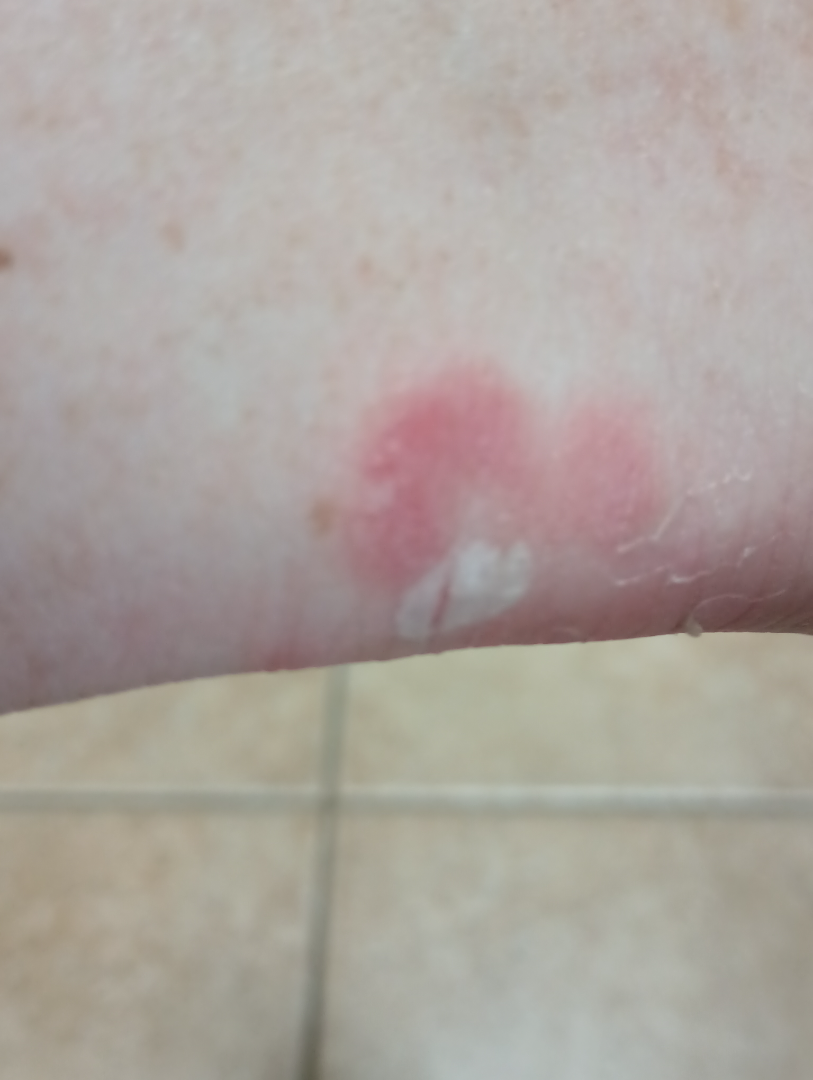<dermatology_case>
  <assessment>could not be assessed</assessment>
  <duration>less than one week</duration>
  <shot_type>close-up</shot_type>
  <symptoms>darkening, enlargement</symptoms>
  <systemic_symptoms>mouth sores</systemic_symptoms>
  <patient>female, age 50–59</patient>
</dermatology_case>